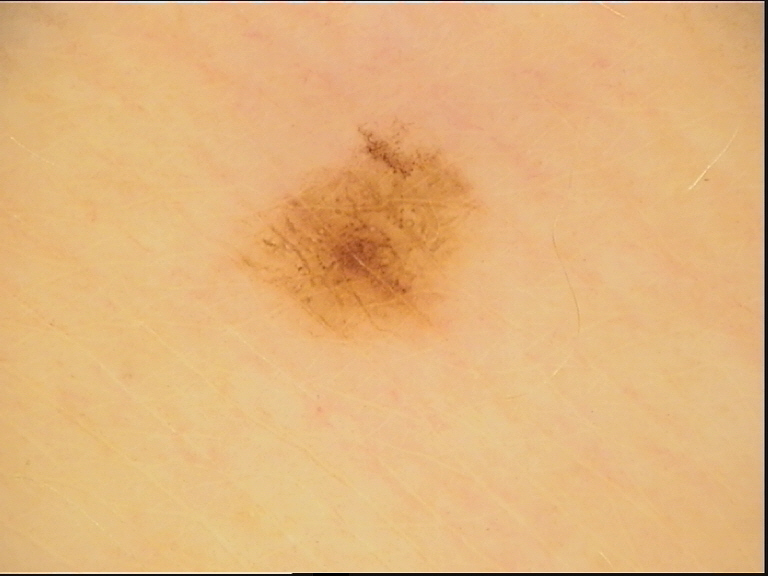Classified as a dysplastic junctional nevus.